A dermoscopic photograph of a skin lesion: 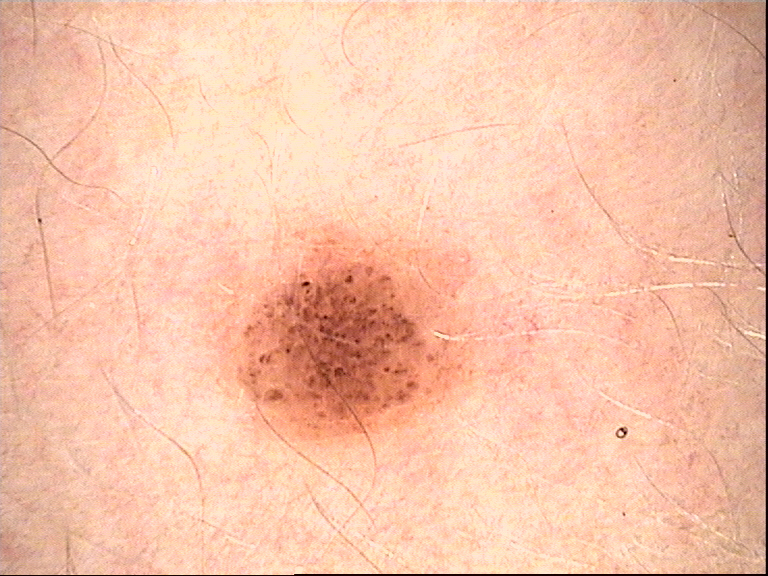Conclusion: Labeled as a dysplastic compound nevus.